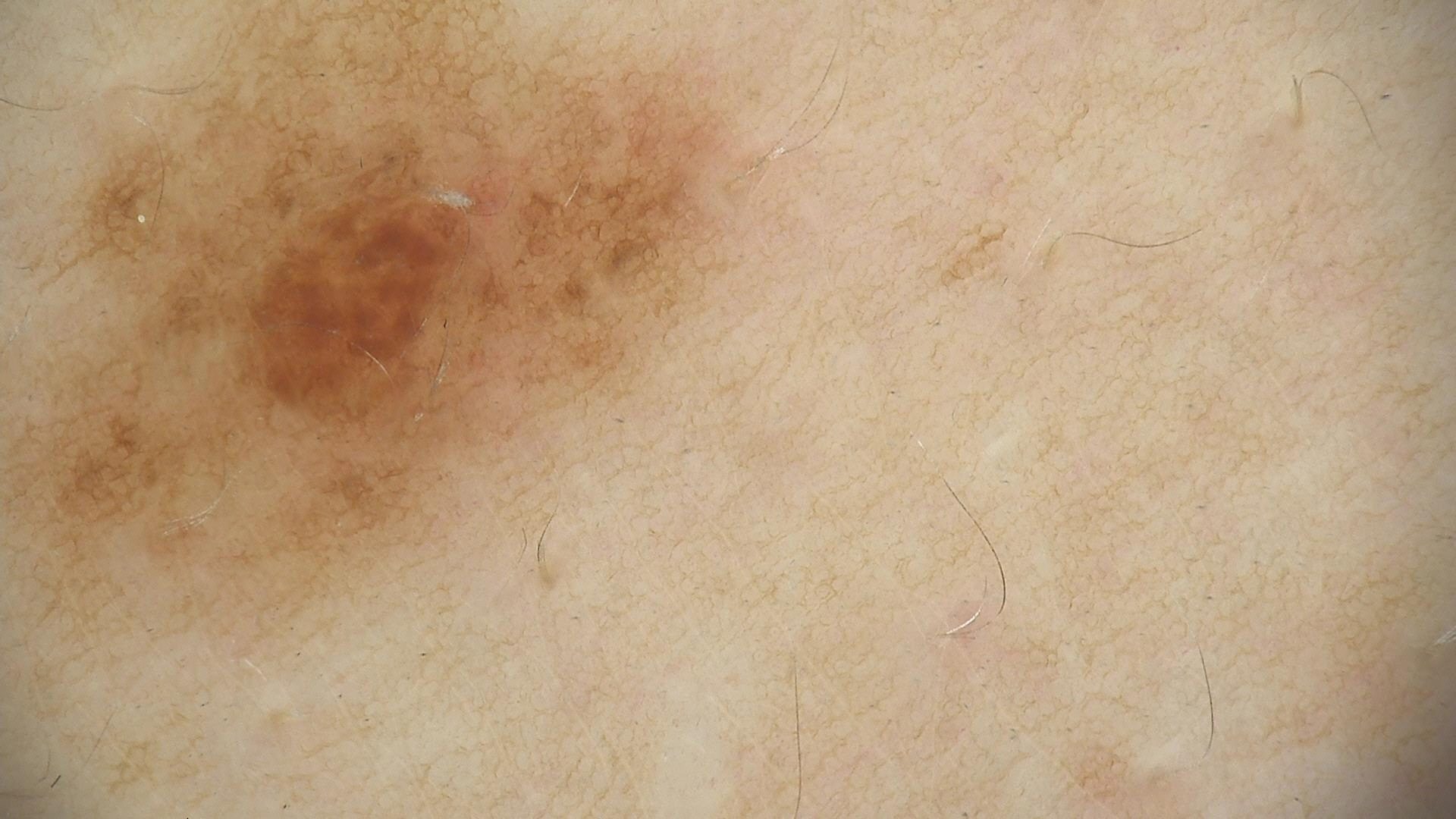A dermoscopic image of a skin lesion. This is a banal lesion. Consistent with a compound nevus.